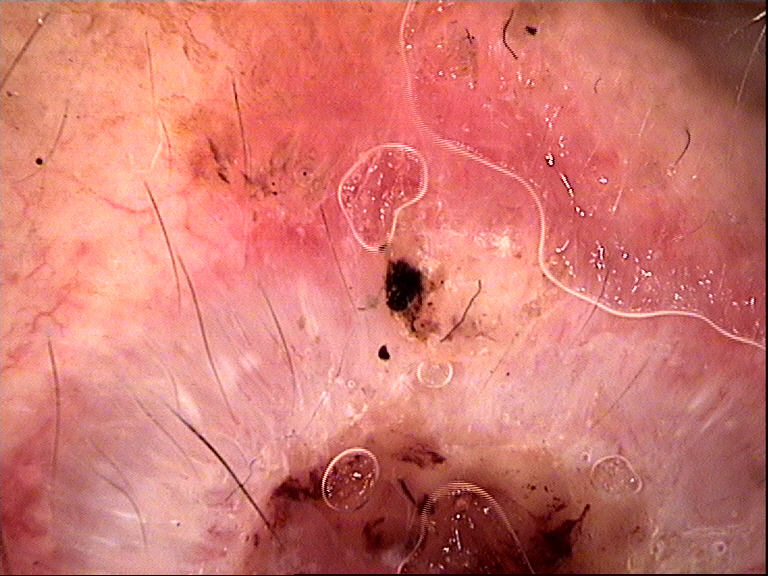{
  "image": "dermatoscopy",
  "diagnosis": {
    "name": "basal cell carcinoma",
    "code": "bcc",
    "malignancy": "malignant",
    "super_class": "non-melanocytic",
    "confirmation": "histopathology"
  }
}